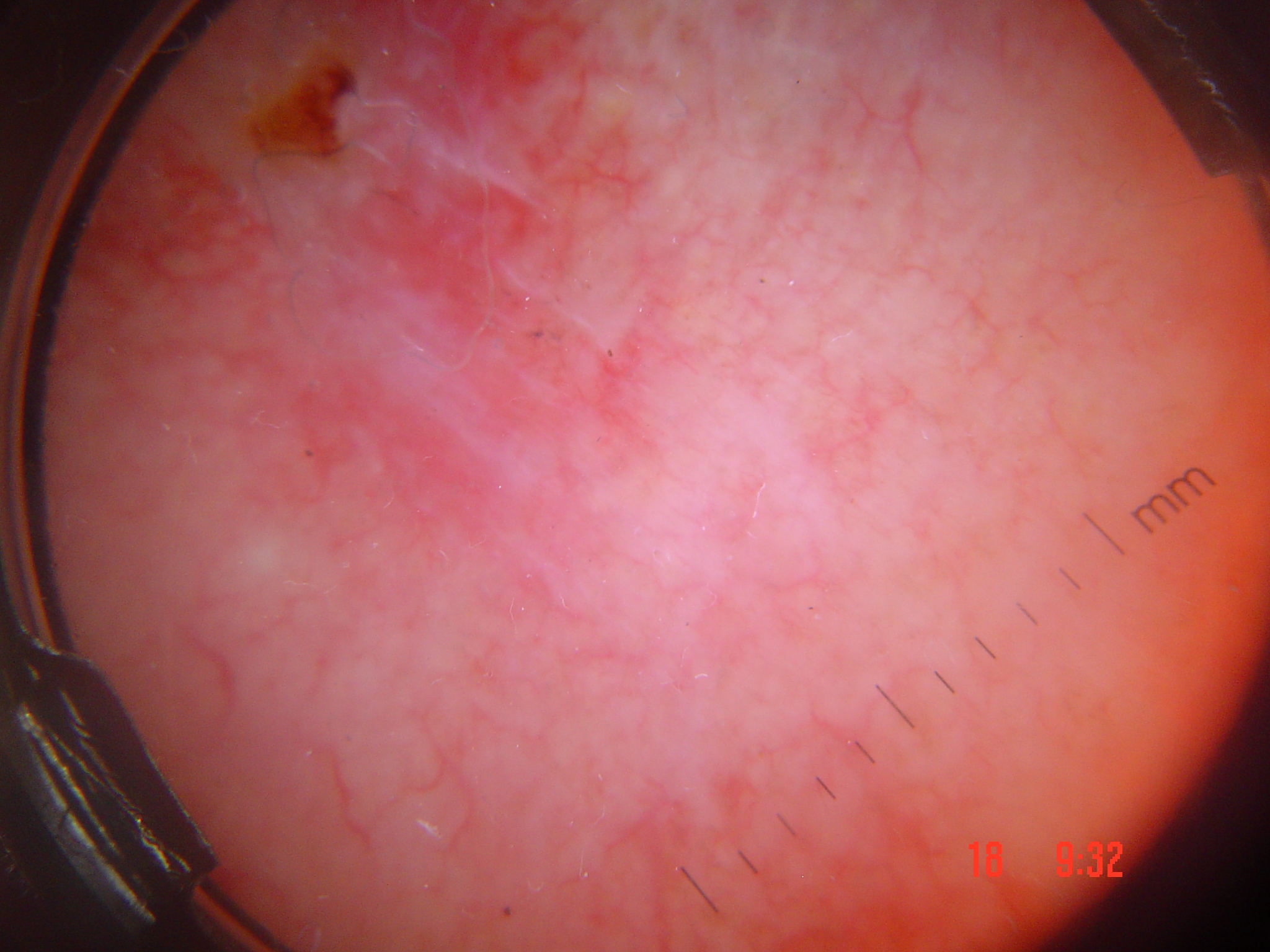| field | value |
|---|---|
| subtype | keratinocytic |
| diagnosis | basal cell carcinoma (biopsy-proven) |